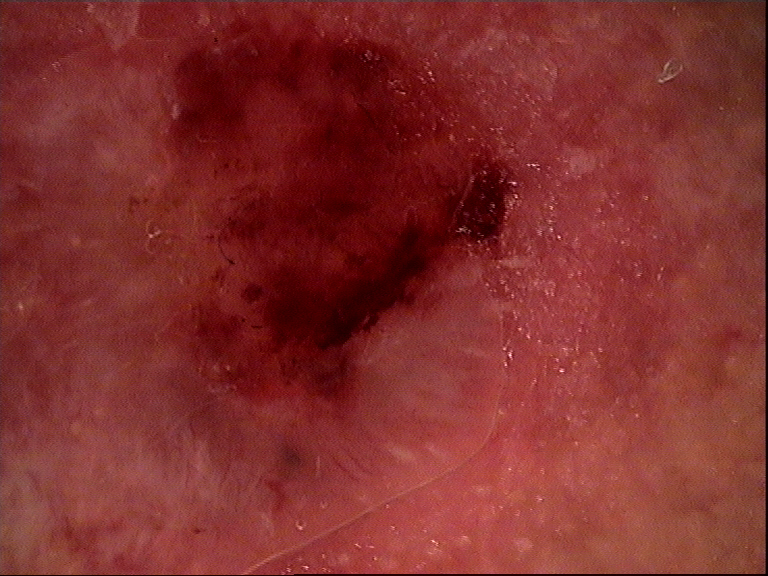{"image": "dermatoscopy", "lesion_type": {"main_class": "keratinocytic"}, "diagnosis": {"name": "basal cell carcinoma", "code": "bcc", "malignancy": "malignant", "super_class": "non-melanocytic", "confirmation": "histopathology"}}